FST IV; the chart records prior skin cancer (patient or family):
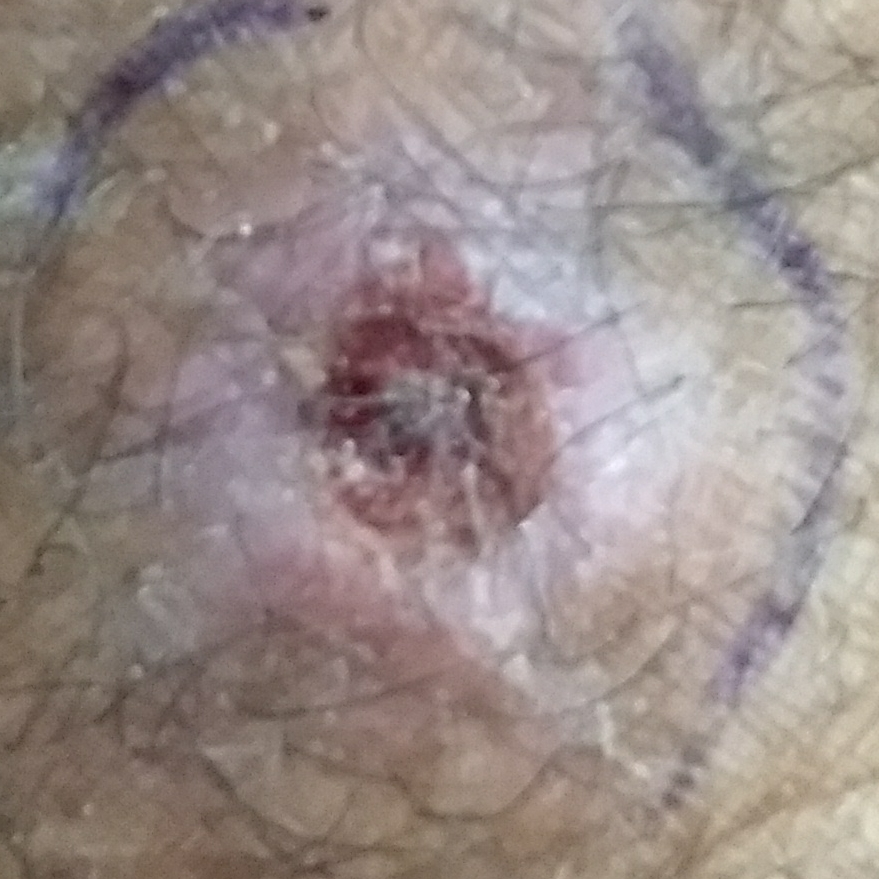Located on a forearm. The lesion measures 13 × 13 mm. The patient describes that the lesion has bled, itches, and is elevated. Histopathology confirmed a squamous cell carcinoma.